A dermoscopic photograph of a skin lesion.
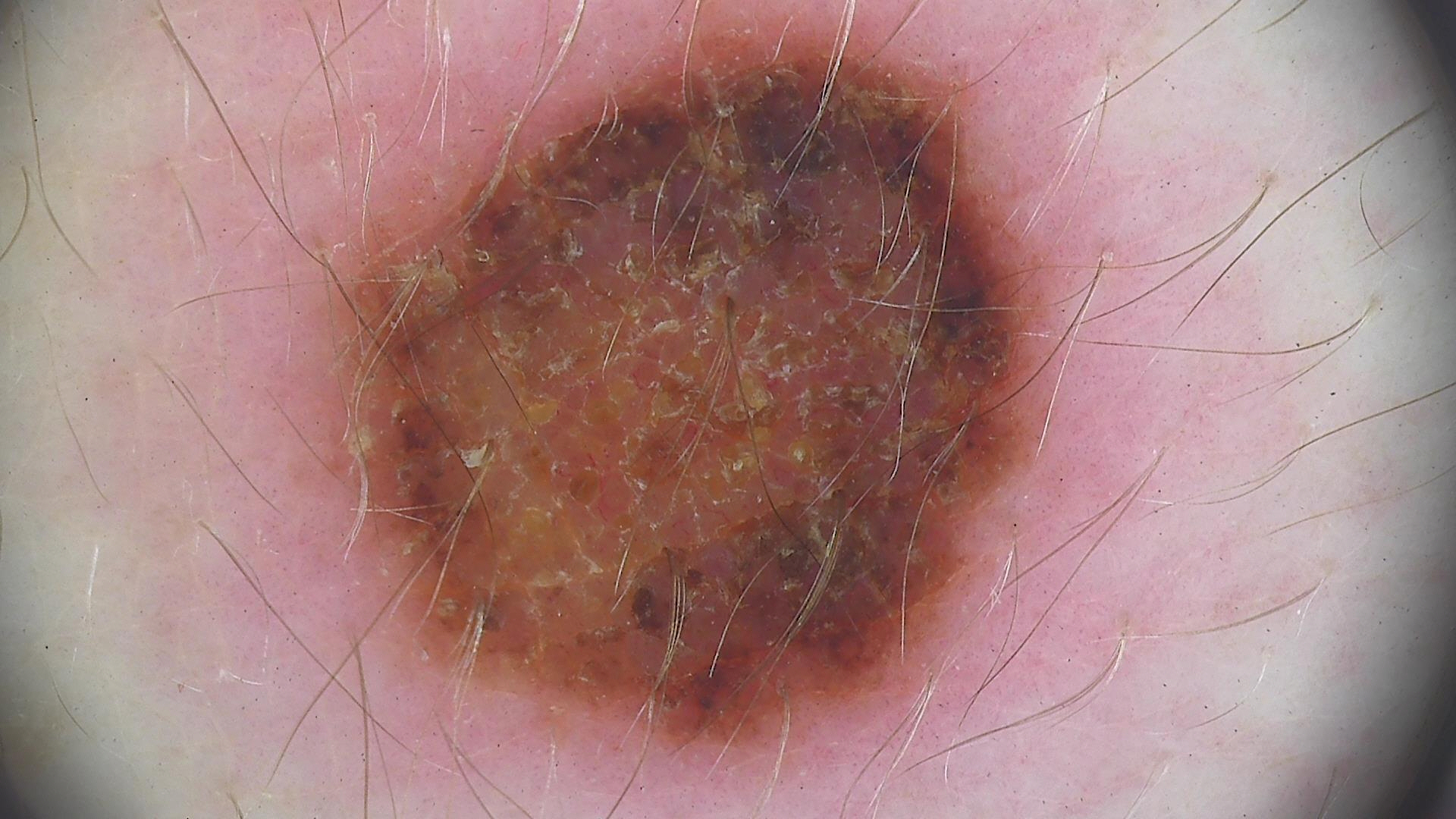This is a banal lesion. Consistent with a congenital compound nevus.